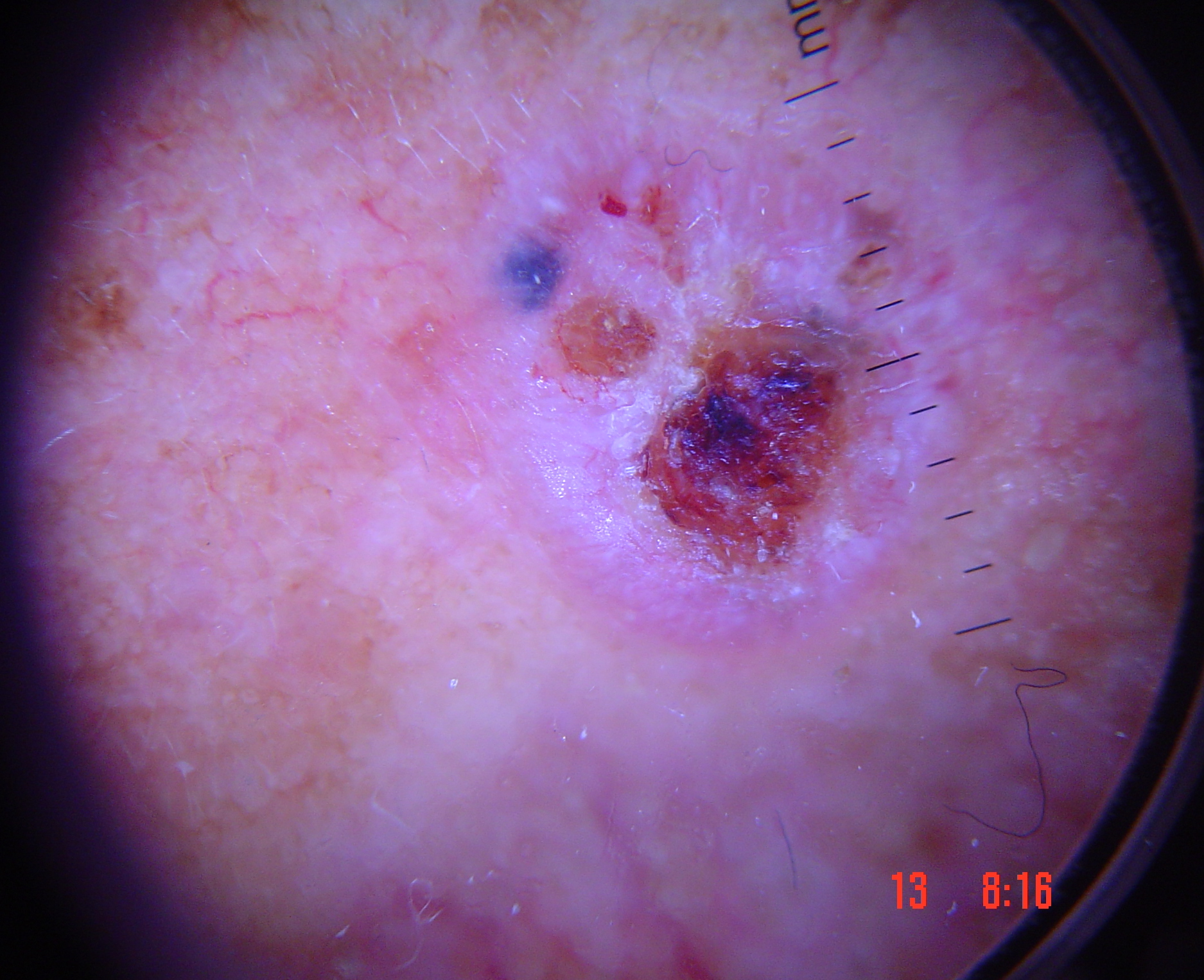A dermoscopic image of a skin lesion. Histopathology confirmed a basal cell carcinoma.